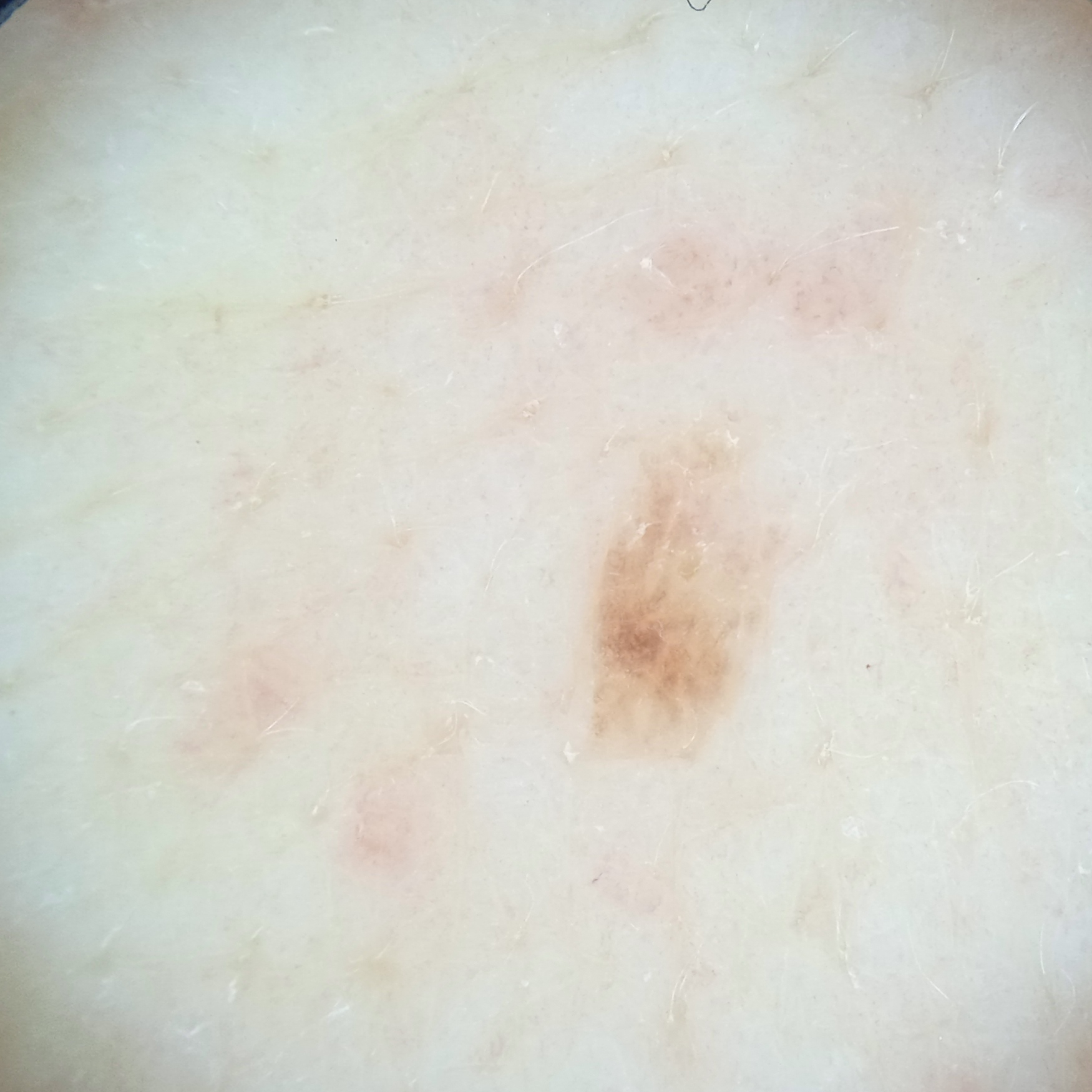modality: dermoscopy
relevant history: a personal history of skin cancer, a personal history of cancer
patient: female, 71 years old
sun reaction: skin reddens with sun exposure
referral context: research study (no referral diagnosis)
nevus count: few melanocytic nevi overall
location: the back
diameter: 3.8 mm
diagnosis: seborrheic keratosis (dermatologist consensus)